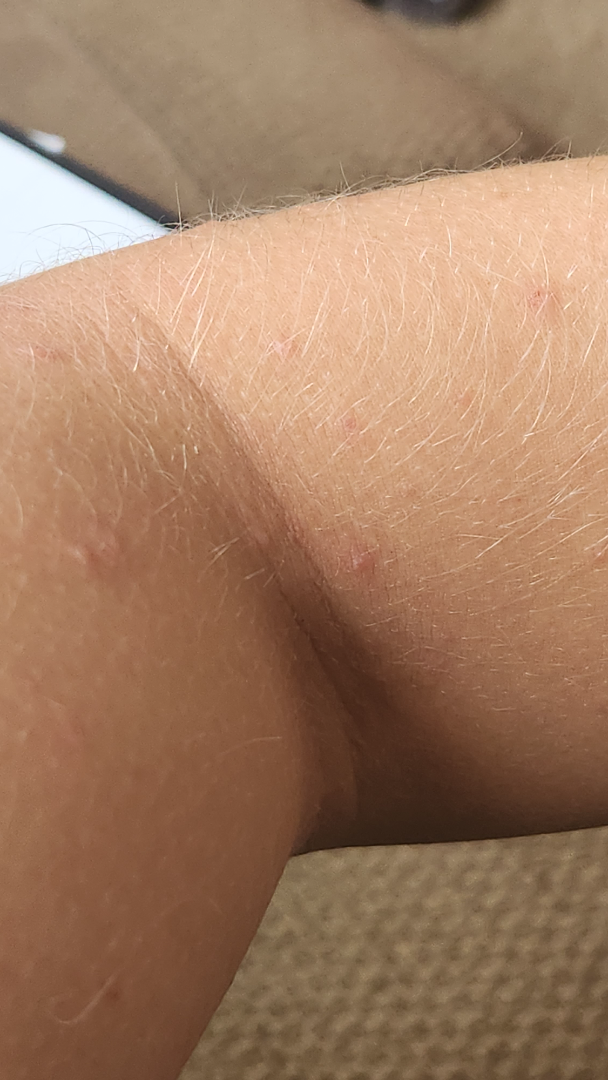Clinical context:
This image was taken at an angle. The affected area is the back of the hand and arm. Reported duration is one to four weeks. The patient is a male aged 18–29. Reported lesion symptoms include itching. The patient considered this a rash.
Assessment:
Scabies (weight 0.54); Insect Bite (weight 0.23); Hypersensitivity (weight 0.23).